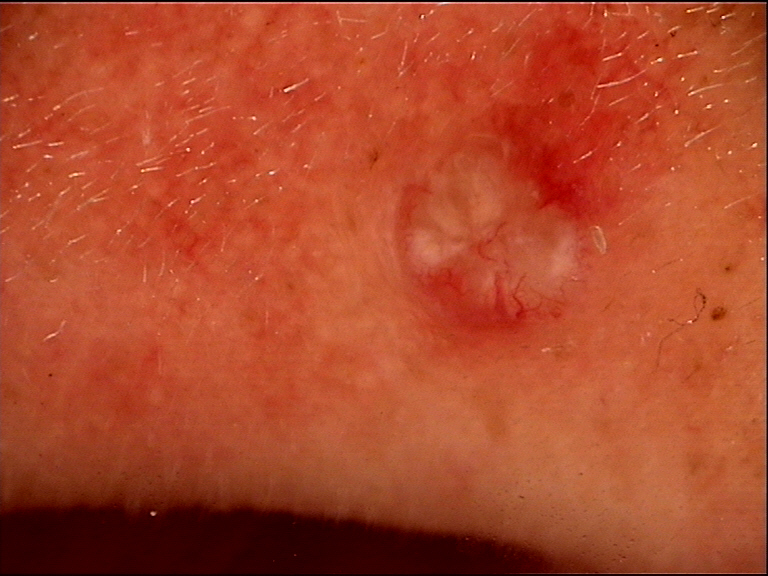Q: What is this lesion?
A: basal cell carcinoma (biopsy-proven)